A dermoscopic photograph of a skin lesion:
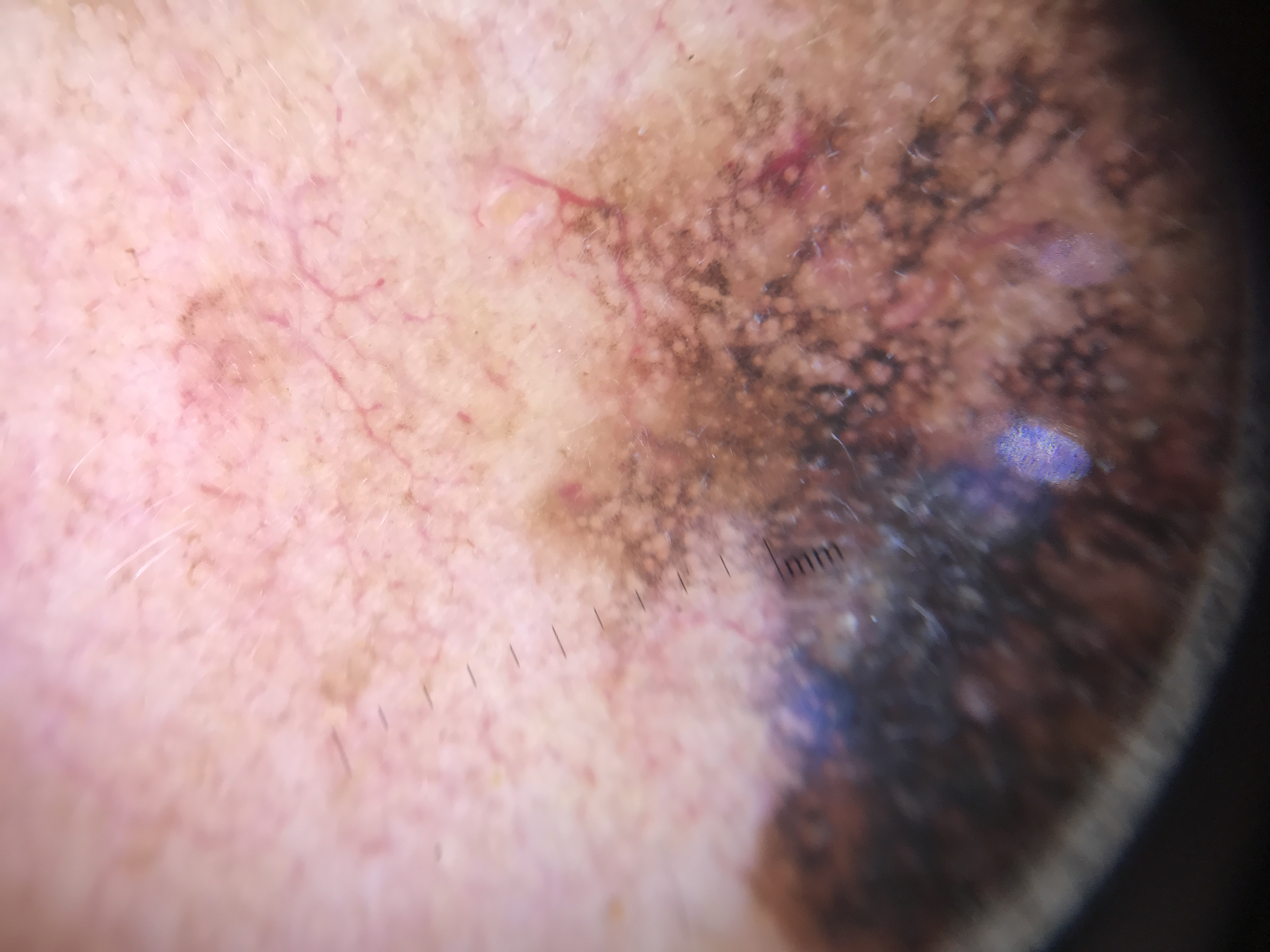Biopsy-confirmed as a lentigo maligna.